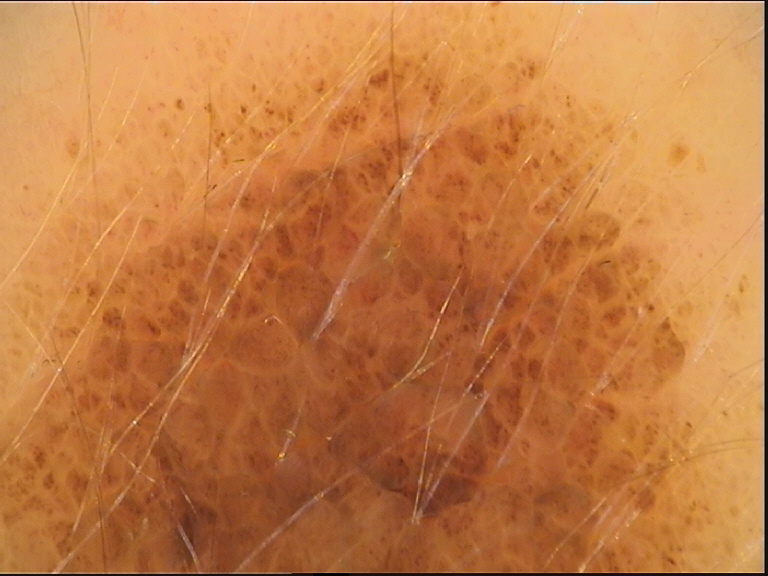{"image": "dermoscopy", "diagnosis": {"name": "congenital compound nevus", "code": "ccb", "malignancy": "benign", "super_class": "melanocytic", "confirmation": "expert consensus"}}